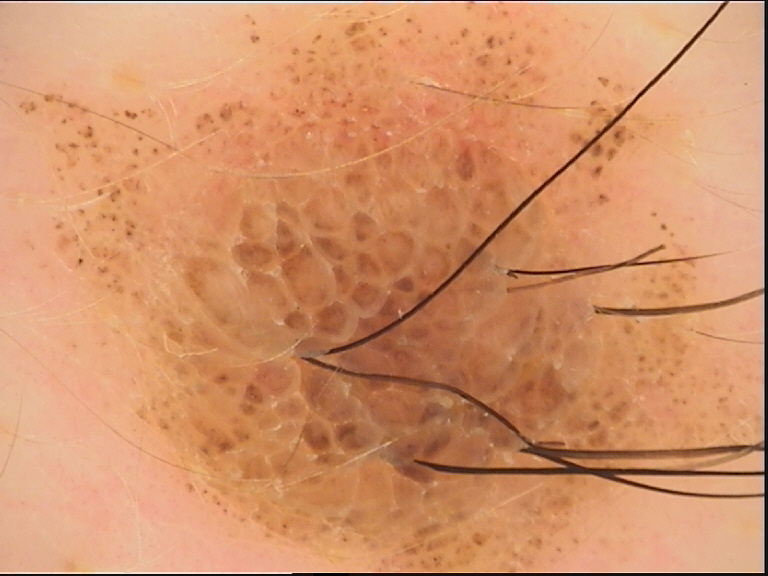• imaging · dermoscopy
• lesion type · banal
• label · compound nevus (expert consensus)